A male patient in their 40s; the patient was assessed as Fitzpatrick III; a dermoscopic close-up of a skin lesion.
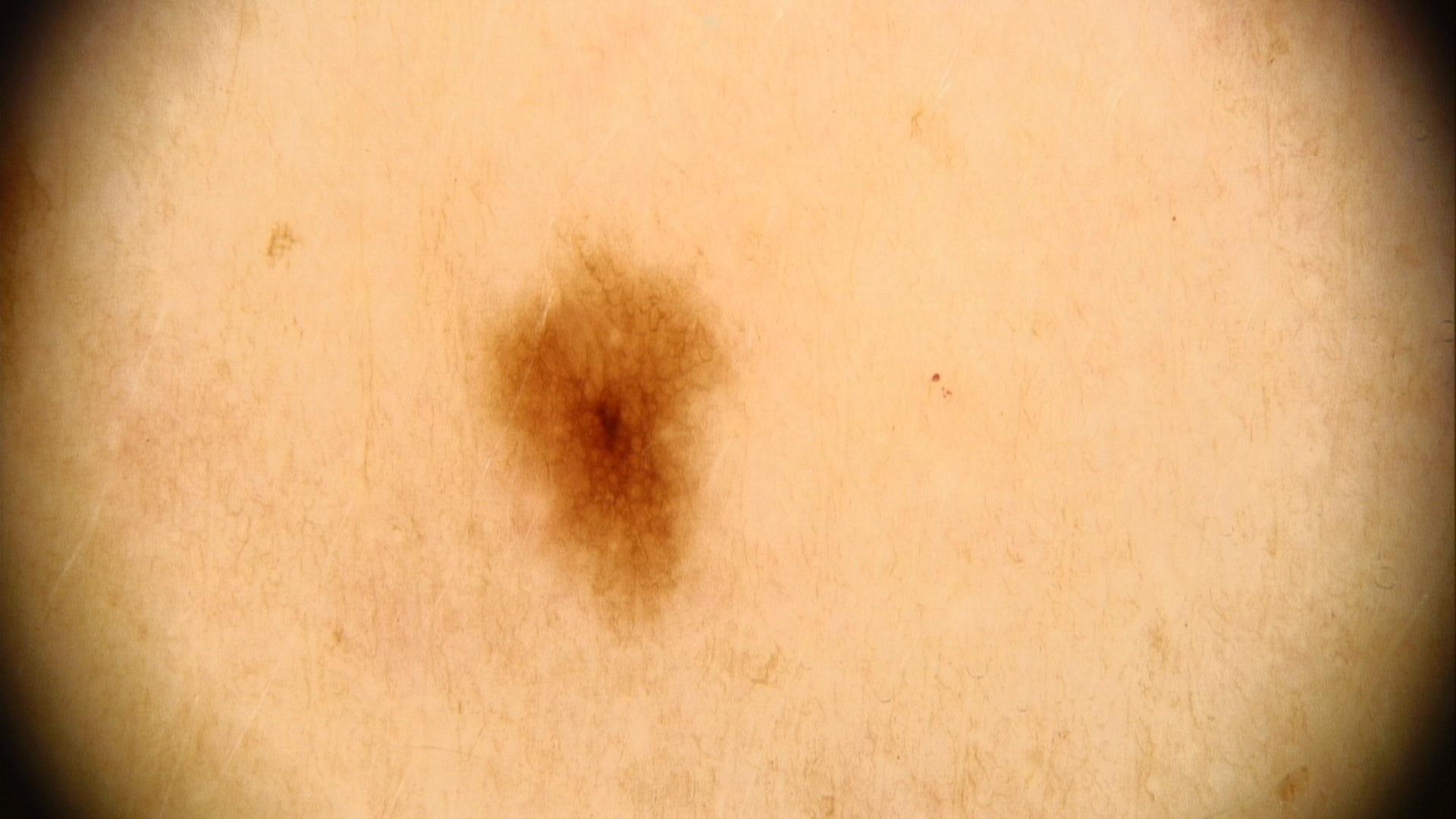lesion_location:
  region: the trunk
  detail: the posterior trunk
diagnosis:
  name: Nevus
  malignancy: benign
  confirmation: expert clinical impression
  lineage: melanocytic